A smartphone photograph of a skin lesion:
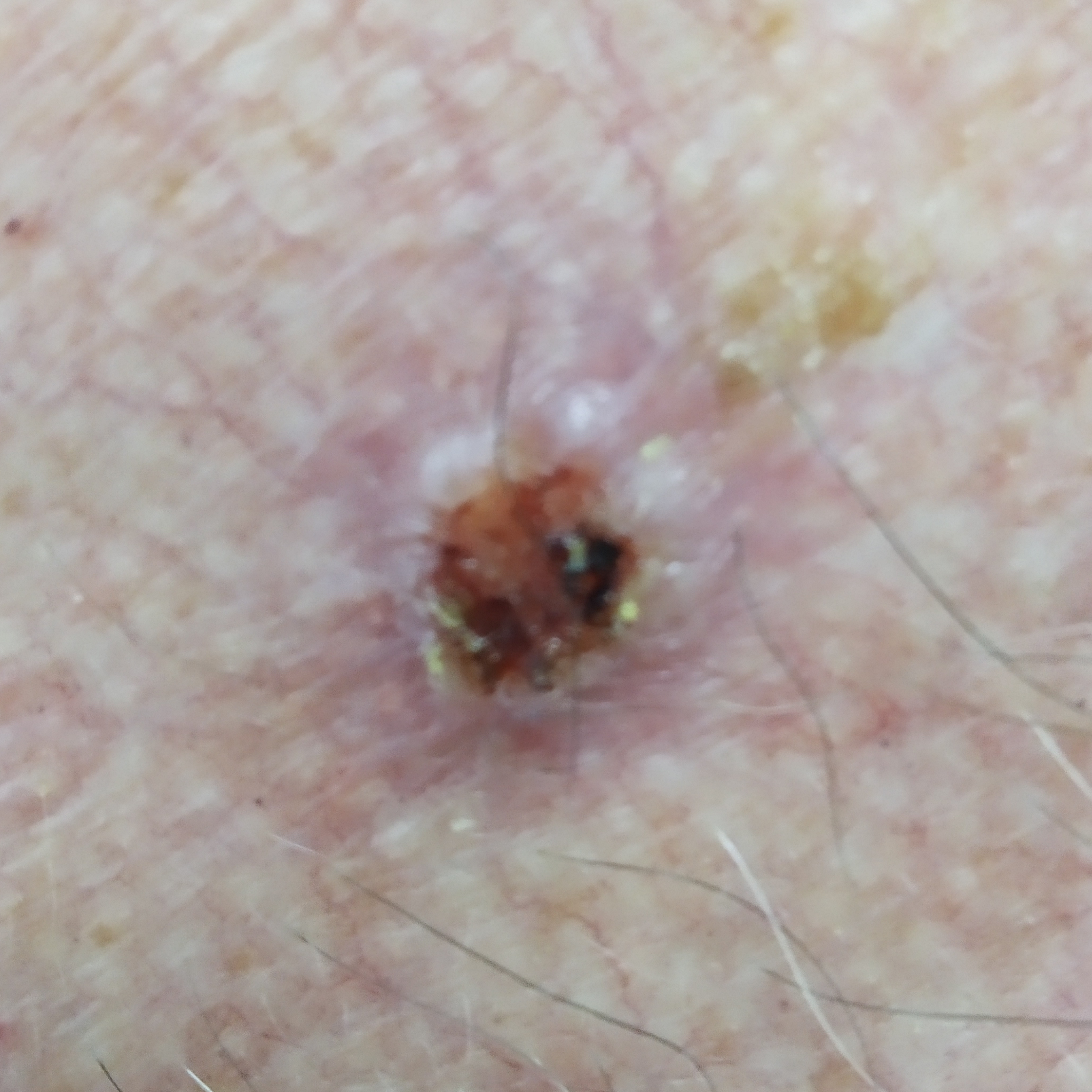Summary: The lesion involves the chest. Per patient report, the lesion itches, has bled, is elevated, and hurts. Diagnosis: Histopathologically confirmed as a basal cell carcinoma.